A close-up photograph: 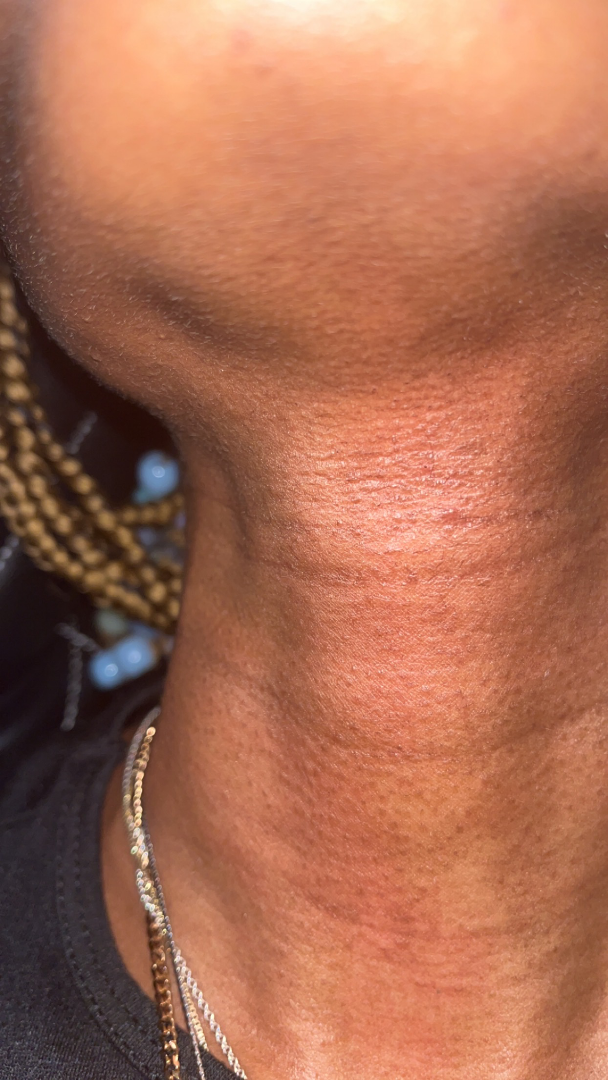Findings: On photographic review, Acne (leading).